A female subject aged 48-52 · a dermoscopic photograph of a skin lesion — 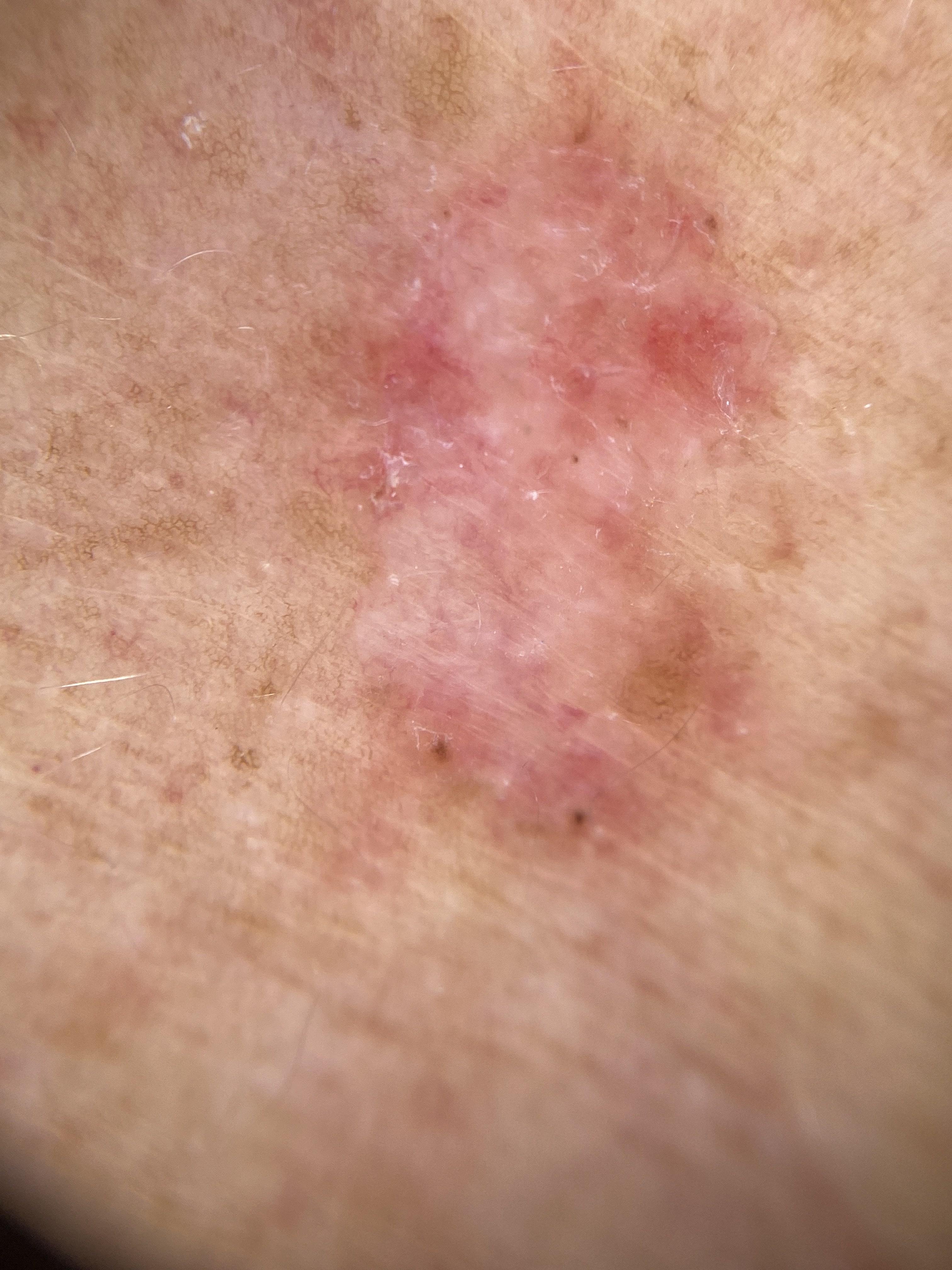On biopsy, the diagnosis was a basal cell carcinoma.